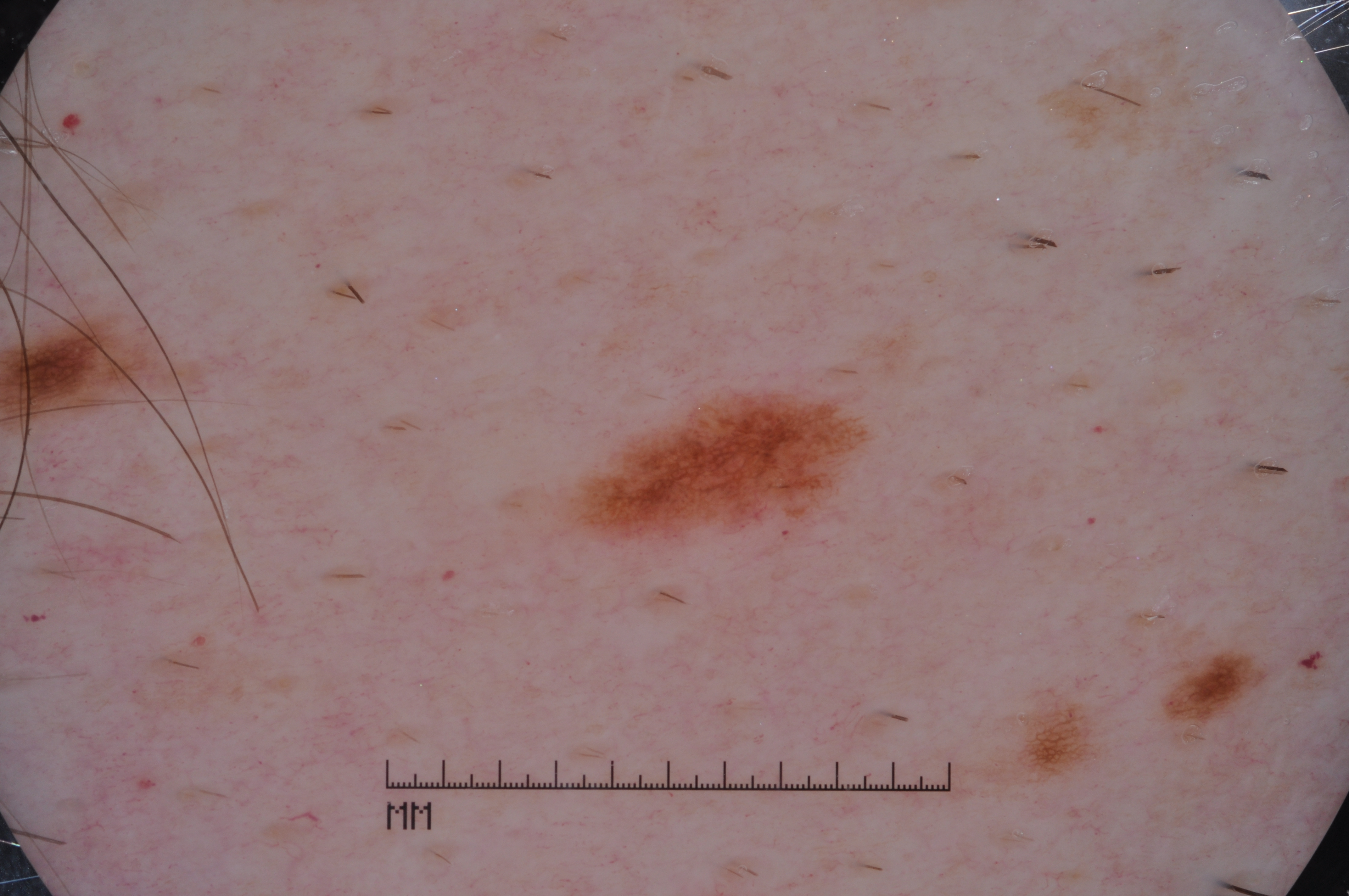image type: dermatoscopic image of a skin lesion; subject: male, aged approximately 60; lesion bbox: [580, 399, 854, 532]; features: pigment network; diagnosis: a melanocytic nevus, a benign lesion.